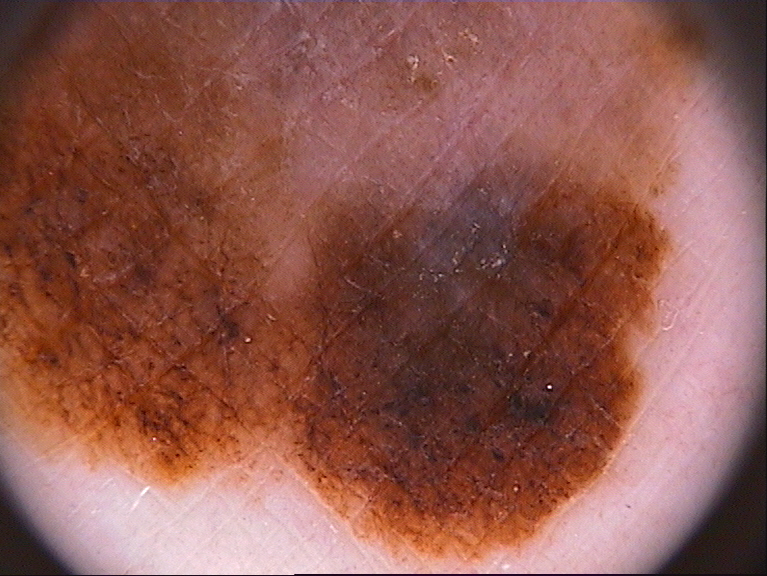Findings:
A skin lesion imaged with a dermatoscope. The lesion extends across almost the whole field of view. Dermoscopic assessment notes globules and pigment network.
Pathology:
On biopsy, the diagnosis was a melanoma.